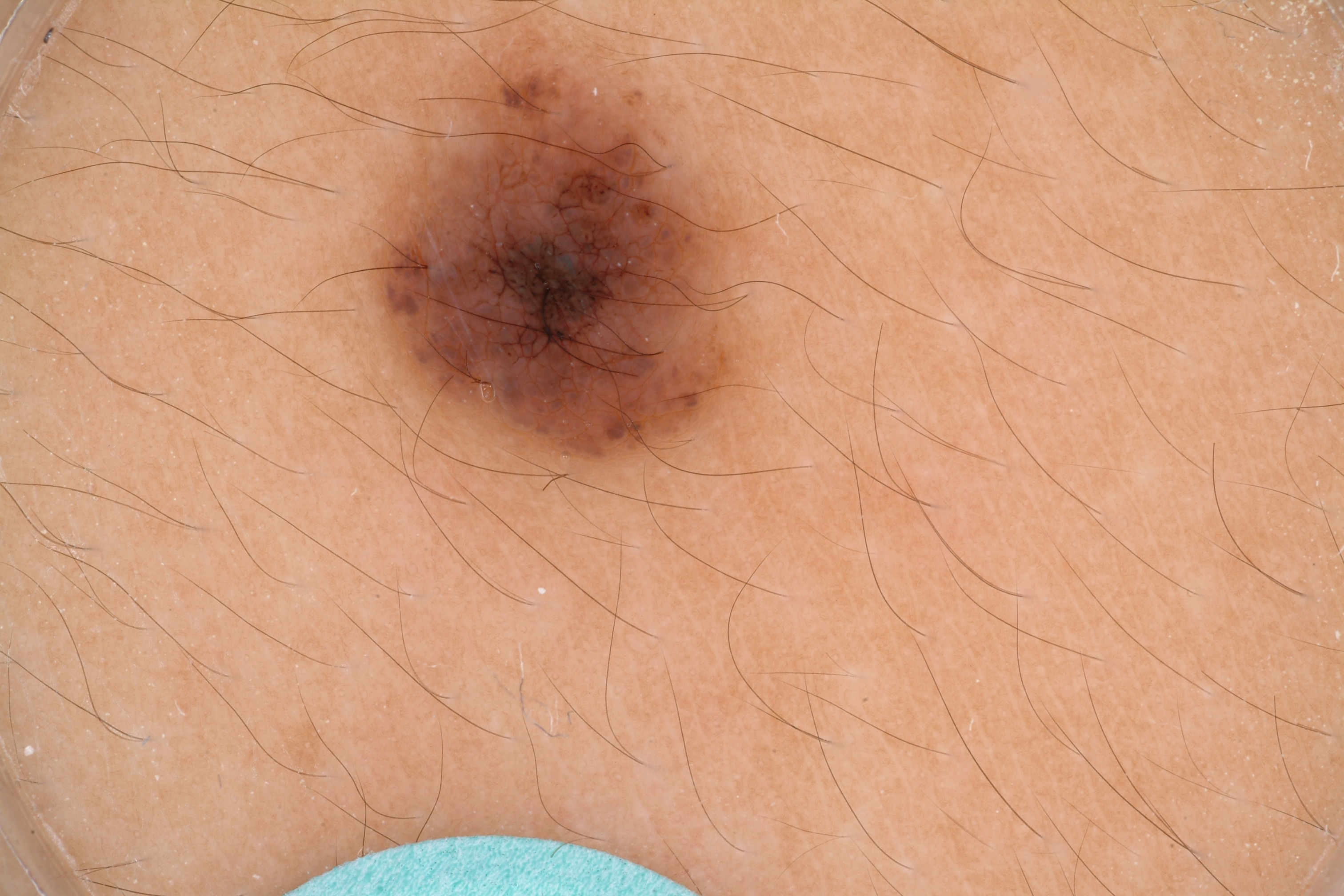Summary: A male subject, about 15 years old. Dermoscopy of a skin lesion. The lesion takes up about 9% of the image. Dermoscopy demonstrates globules and pigment network, with no negative network, milia-like cysts, or streaks. In (x1, y1, x2, y2) order, the lesion is bounded by box(368, 57, 736, 483). Conclusion: The clinical diagnosis was a melanocytic nevus, a benign lesion.